A dermatoscopic image of a skin lesion: 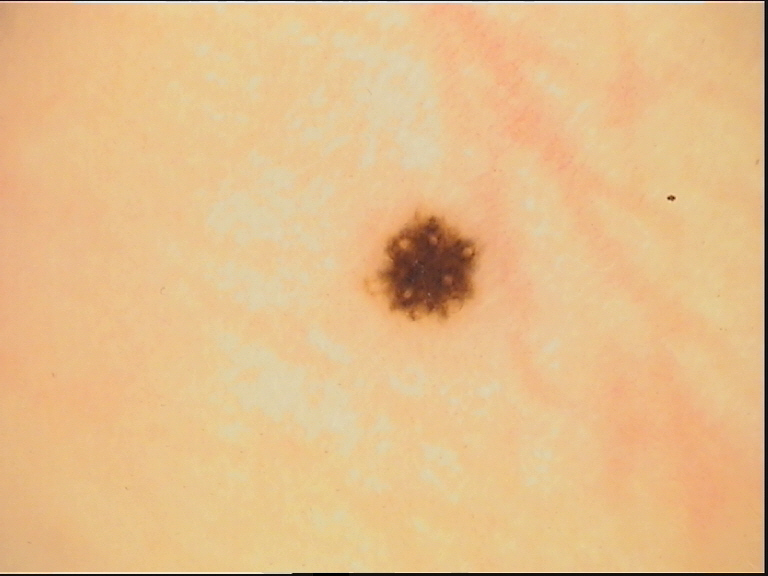{
  "diagnosis": {
    "name": "acral dysplastic junctional nevus",
    "code": "ajd",
    "malignancy": "benign",
    "super_class": "melanocytic",
    "confirmation": "expert consensus"
  }
}